A dermoscopy image of a single skin lesion: 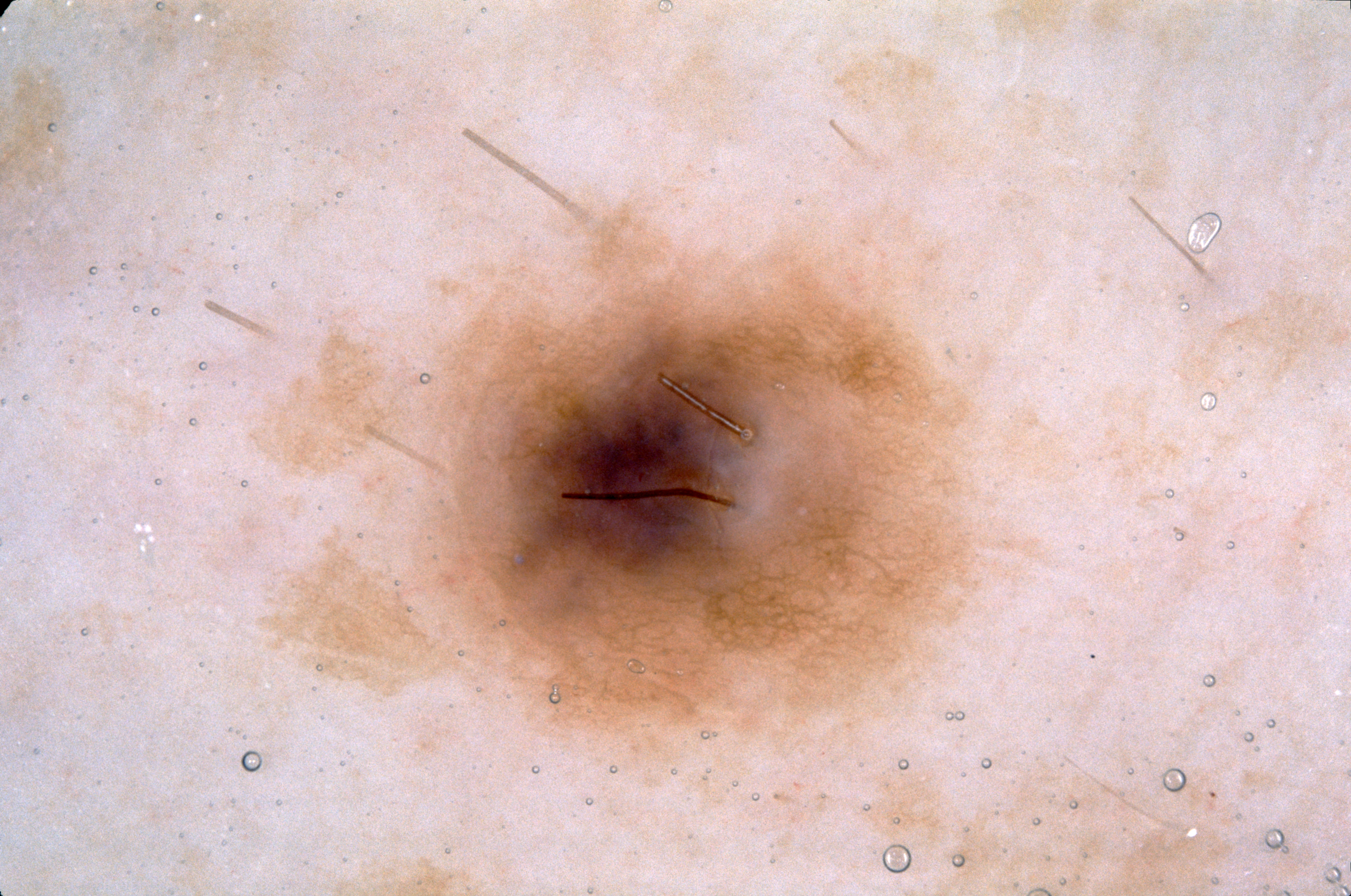Q: What dermoscopic features are present?
A: pigment network
Q: Where is the lesion located?
A: bbox=[404, 205, 967, 734]
Q: What is the diagnosis?
A: a melanocytic nevus, a benign lesion